A dermoscopic close-up of a skin lesion: 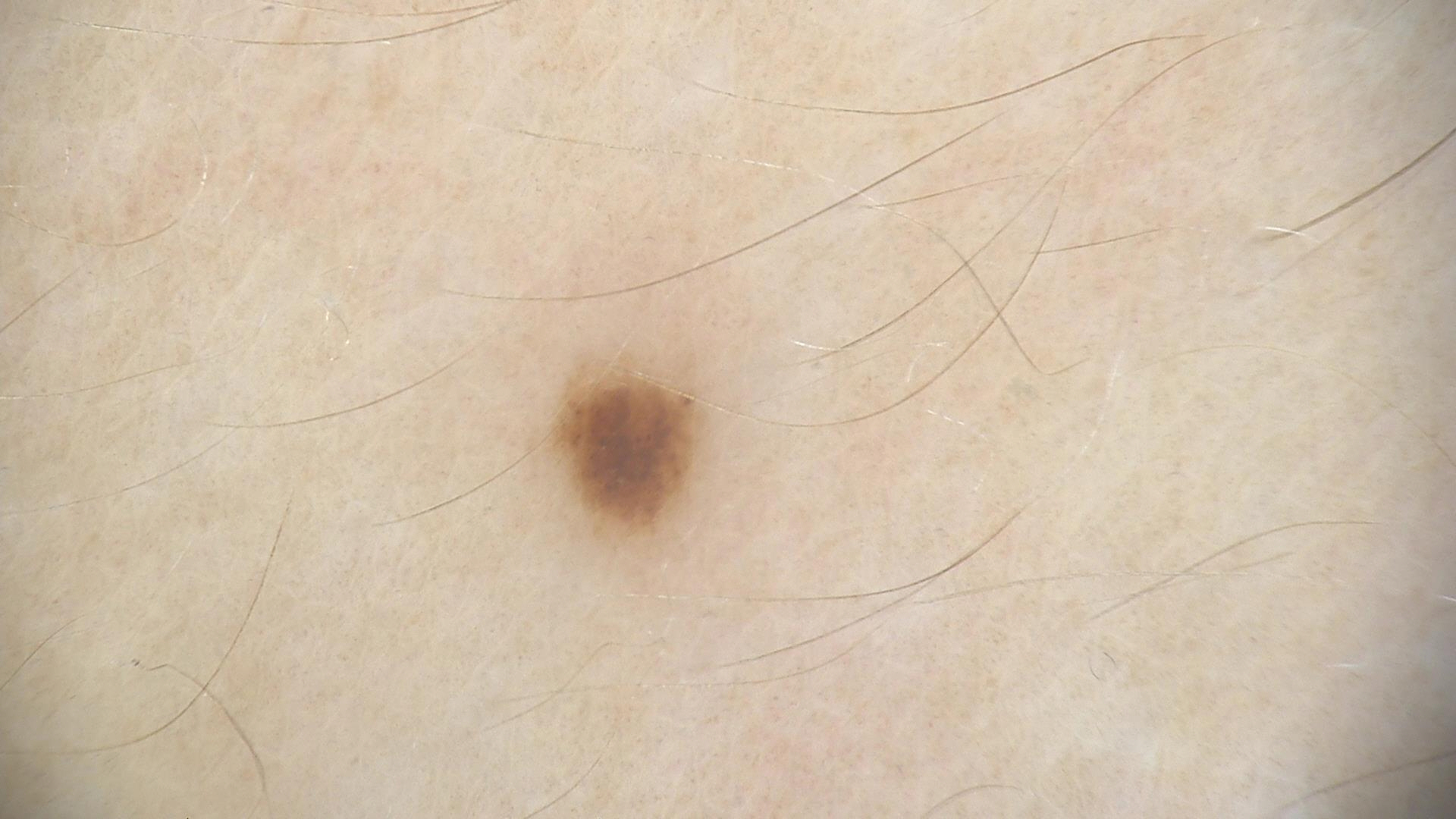assessment — dysplastic junctional nevus (expert consensus)